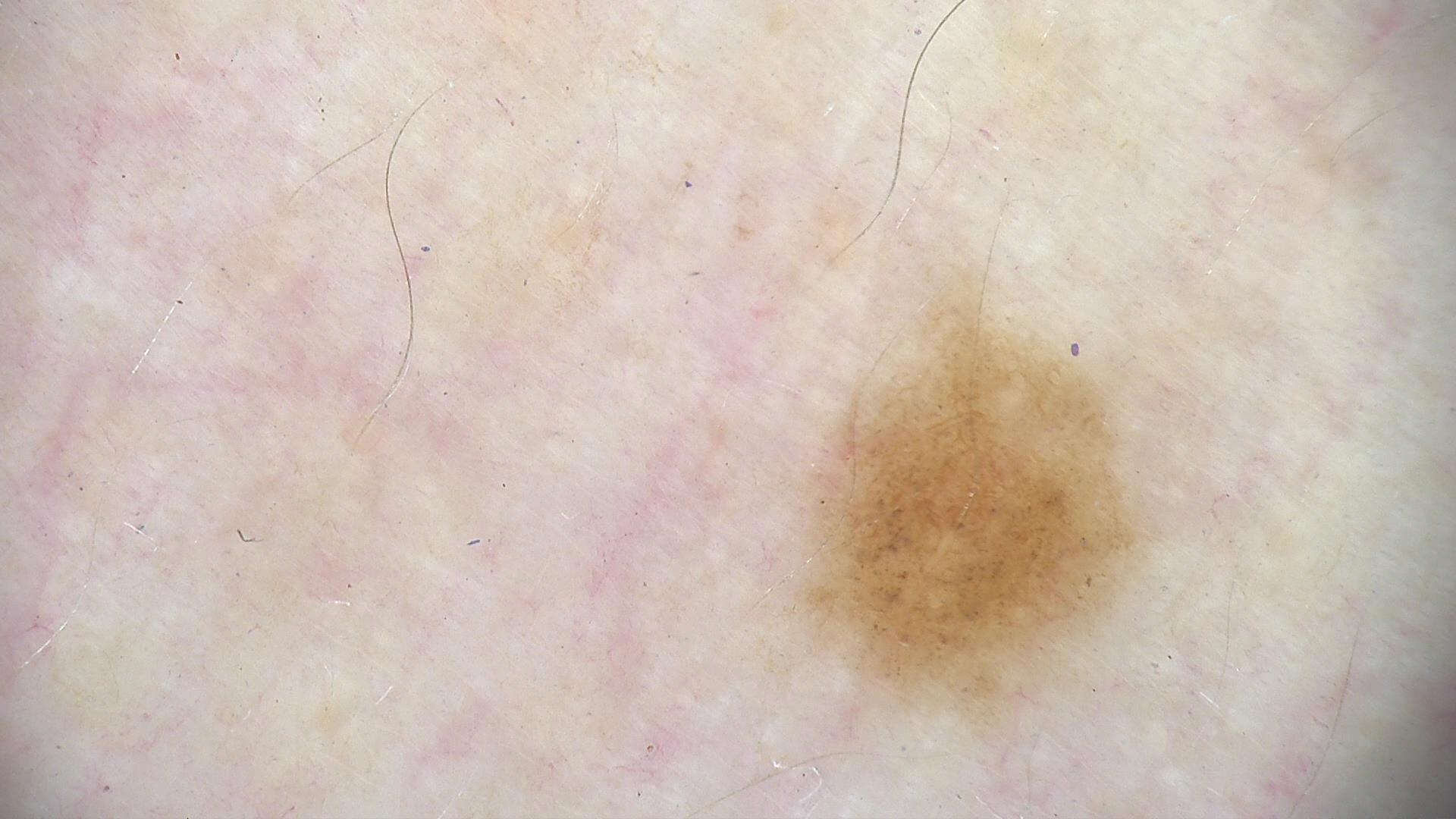imaging=dermoscopy
class=dysplastic junctional nevus (expert consensus)